A female patient approximately 45 years of age. The chart documents no previous melanoma and no melanoma in first-degree relatives. A dermoscopic photograph of a skin lesion. The patient was assessed as Fitzpatrick phototype II.
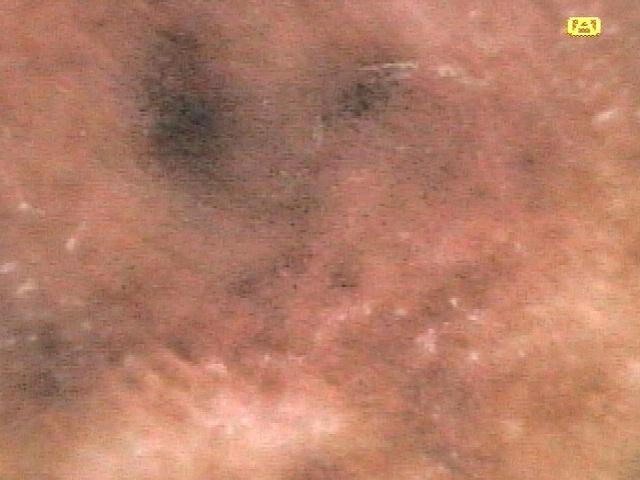Findings:
- site — a lower extremity
- diagnosis — Dermatofibroma (biopsy-proven)